The contributor is 30–39, female. The photo was captured at an angle. The leg is involved. The condition has been present for more than one year. No constitutional symptoms were reported. The contributor reports itching and bothersome appearance. Texture is reported as raised or bumpy and rough or flaky. The patient described the issue as a rash.
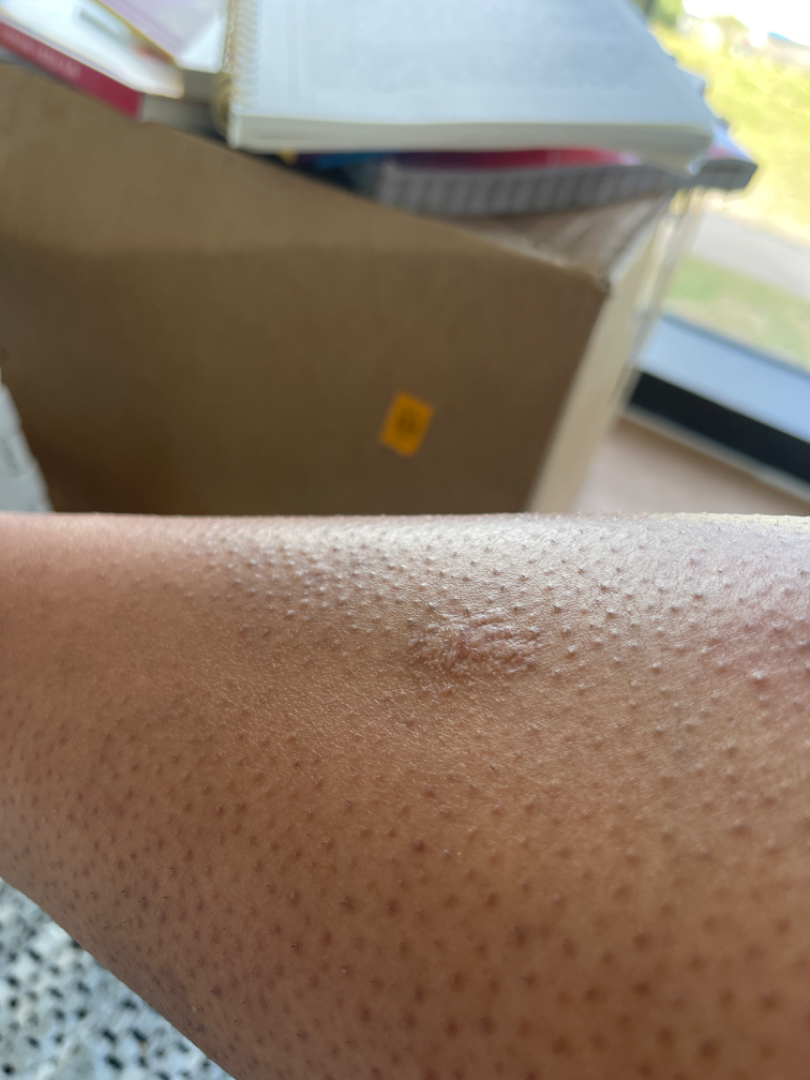The leading consideration is Verruca vulgaris; also raised was SK/ISK.